A male subject 77 years of age; acquired for a research image collection, with no referral diagnosis; the patient says their skin reddens with sun exposure; on a questionnaire the patient reported a personal history of skin cancer and a personal history of cancer; the patient describes having a moderate number of moles; a clinical photograph showing a skin lesion:
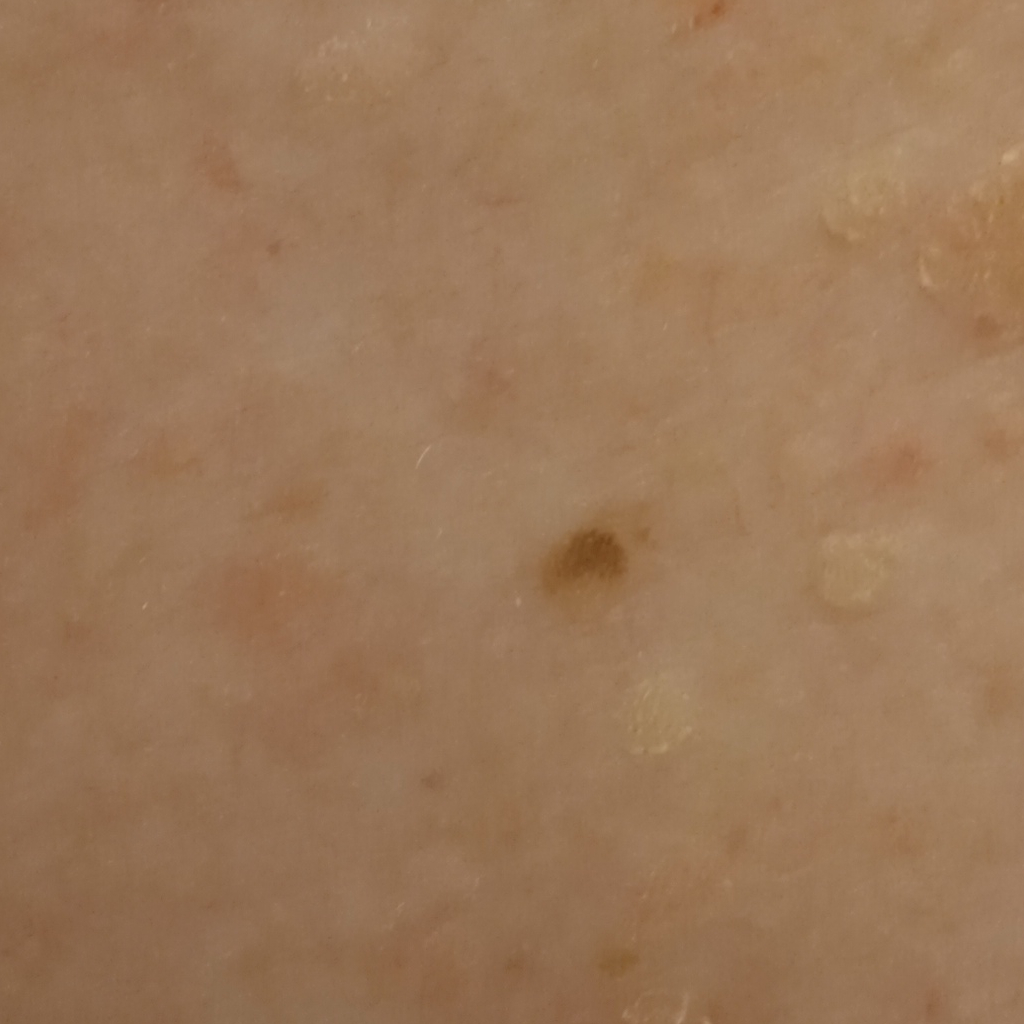Located on the back. Measuring roughly 3 mm. The lesion was assessed as a seborrheic keratosis.